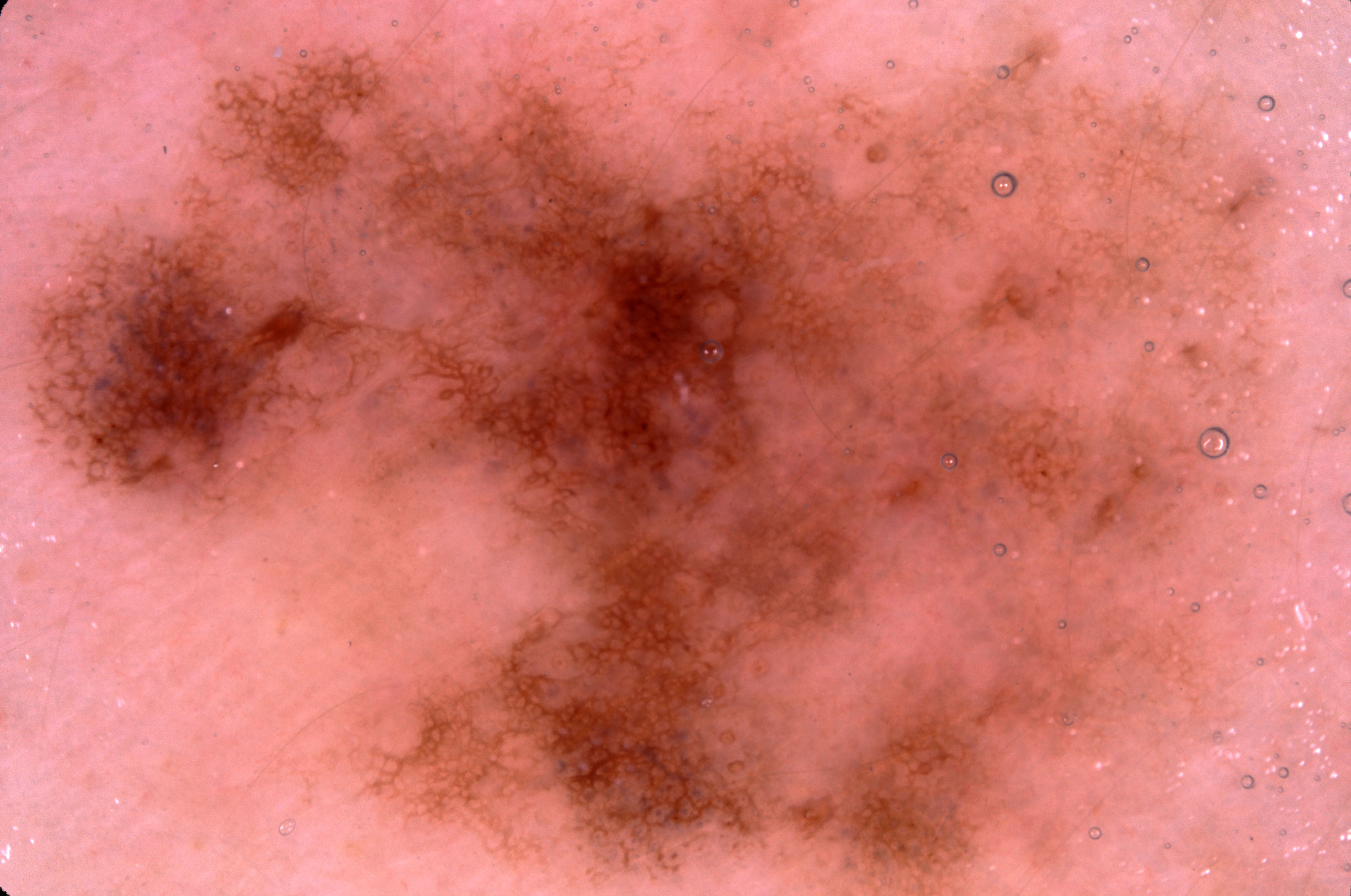A dermoscopic view of a skin lesion. The visible lesion spans x1=32, y1=42, x2=1277, y2=895. Diagnosed as a melanocytic nevus.